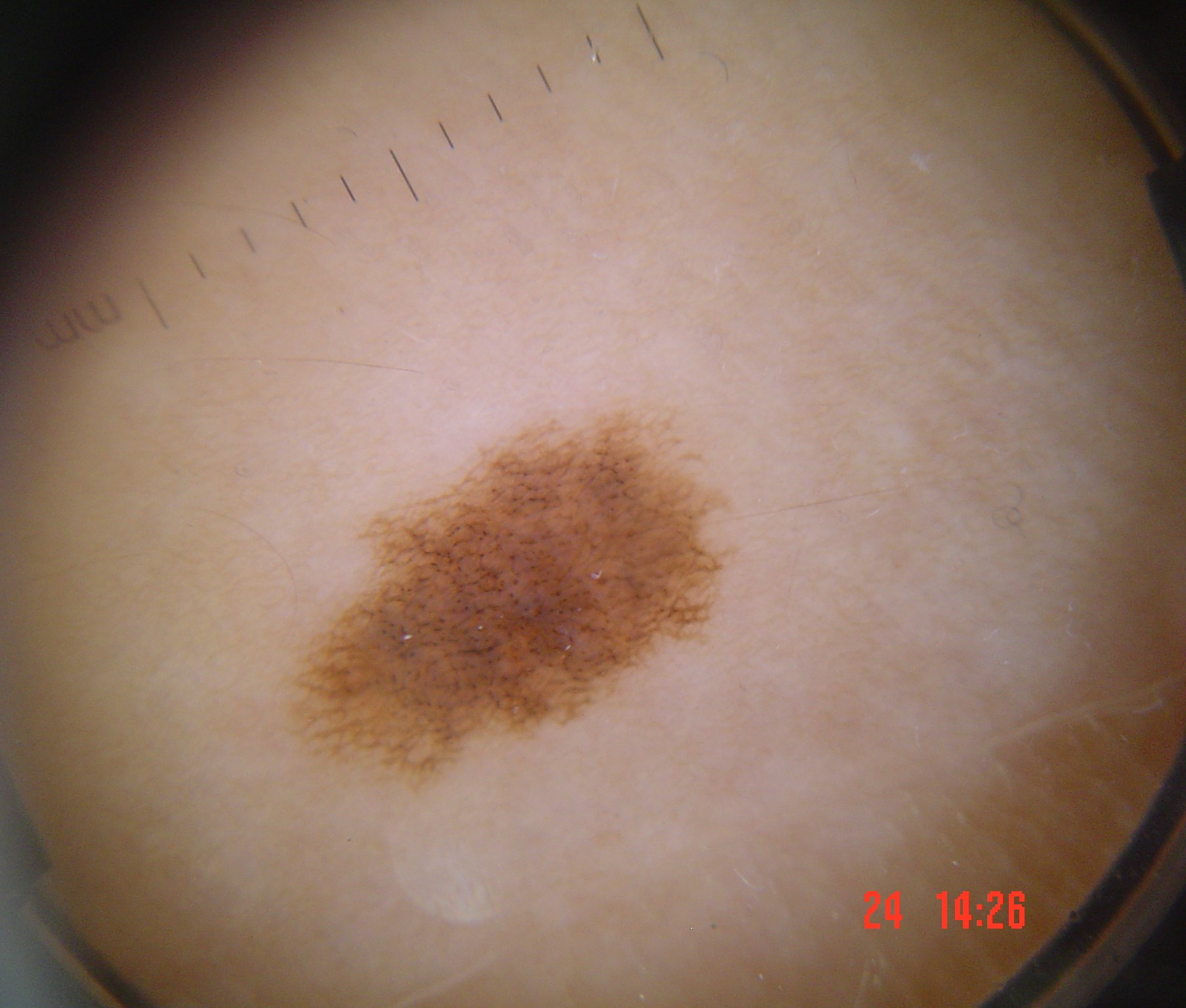Diagnosed as a benign lesion — a dysplastic junctional nevus.